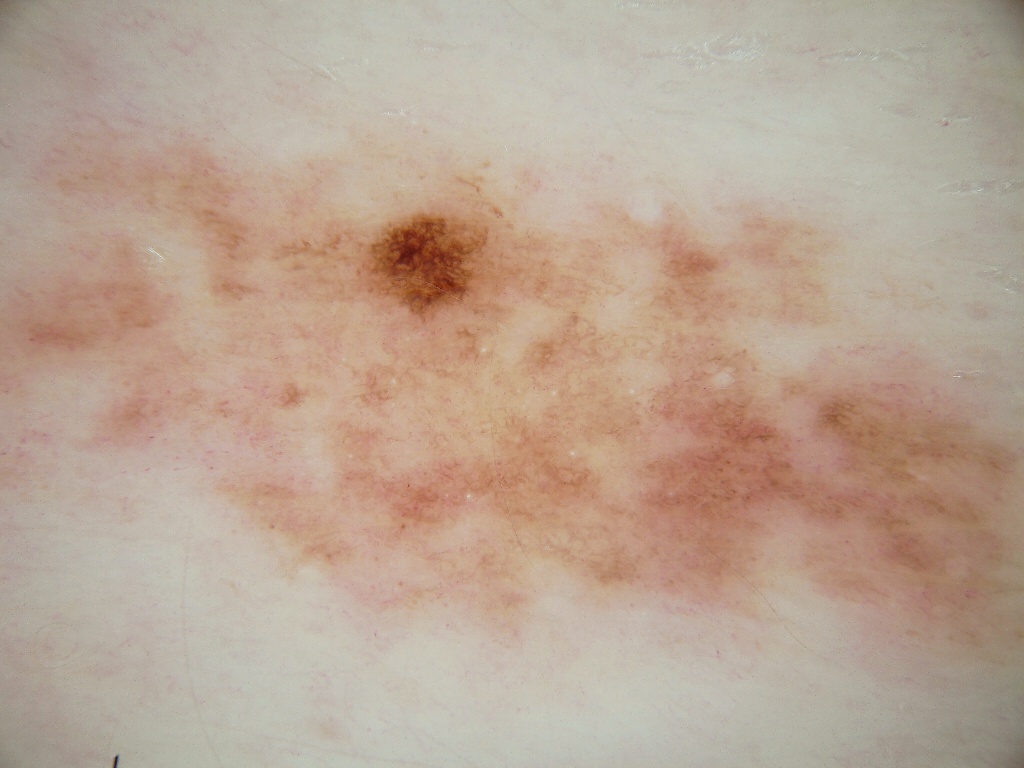A dermoscopic close-up of a skin lesion. The lesion reaches the border of the frame. On dermoscopy, the lesion shows pigment network; no streaks, globules, negative network, or milia-like cysts. Lesion location: <bbox>0, 106, 1018, 698</bbox>. A large lesion occupying much of the field. Diagnosed as a melanocytic nevus.